A female subject aged around 40; a skin lesion imaged with a dermatoscope.
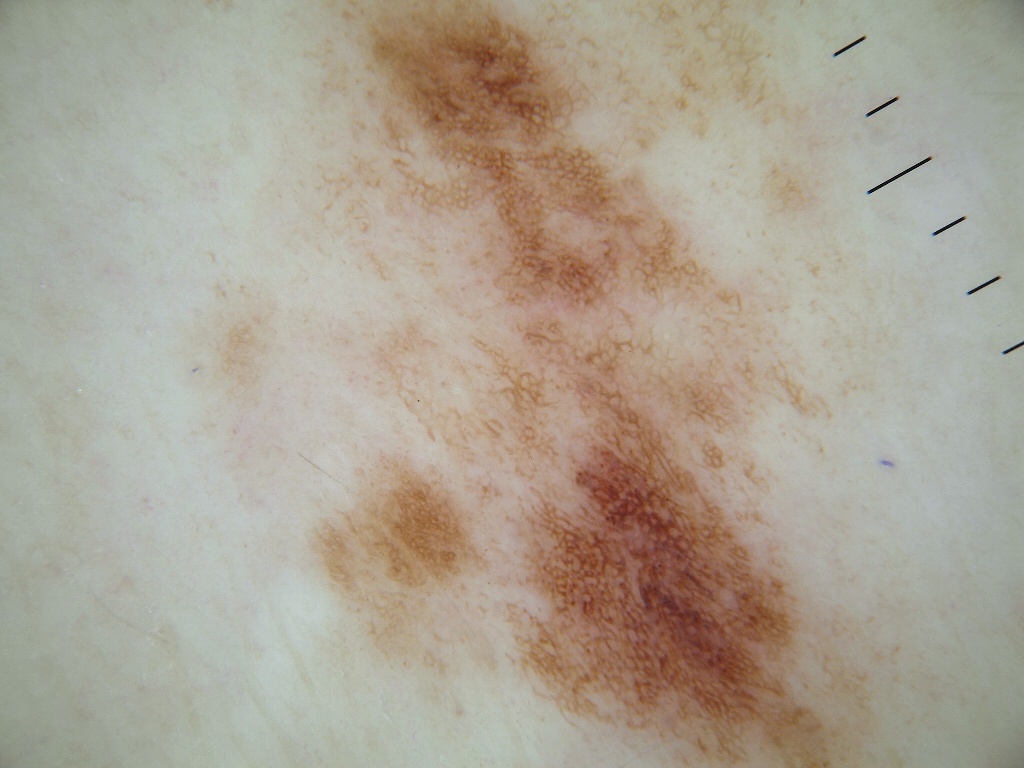Dermoscopy demonstrates pigment network. As (left, top, right, bottom), the lesion's extent is bbox=[183, 3, 973, 765]. Expert review diagnosed this as a melanocytic nevus.